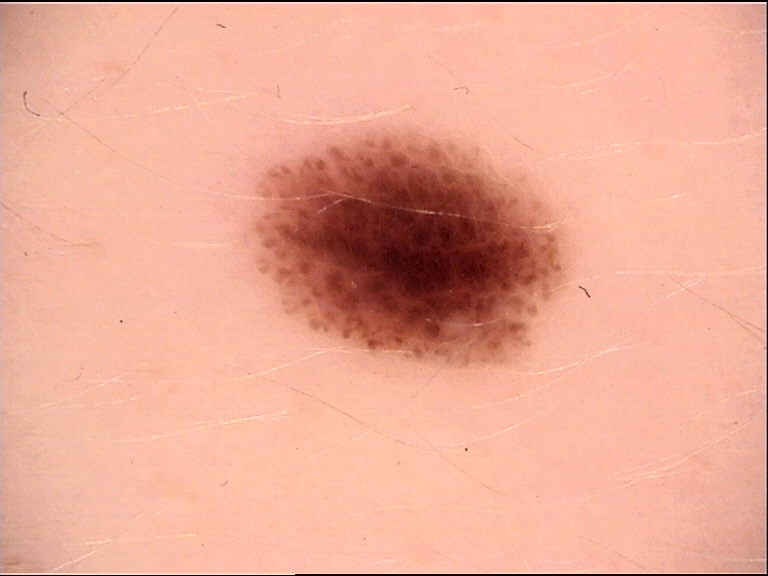A dermoscopic photograph of a skin lesion.
The diagnosis was a benign lesion — a dysplastic junctional nevus.